A dermoscopic photograph of a skin lesion: 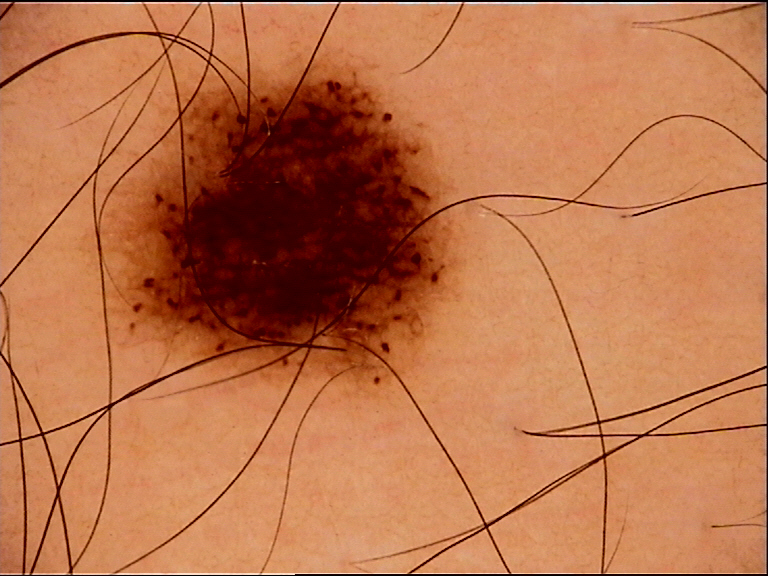Impression: Consistent with a dysplastic junctional nevus.